The photograph was taken at a distance:
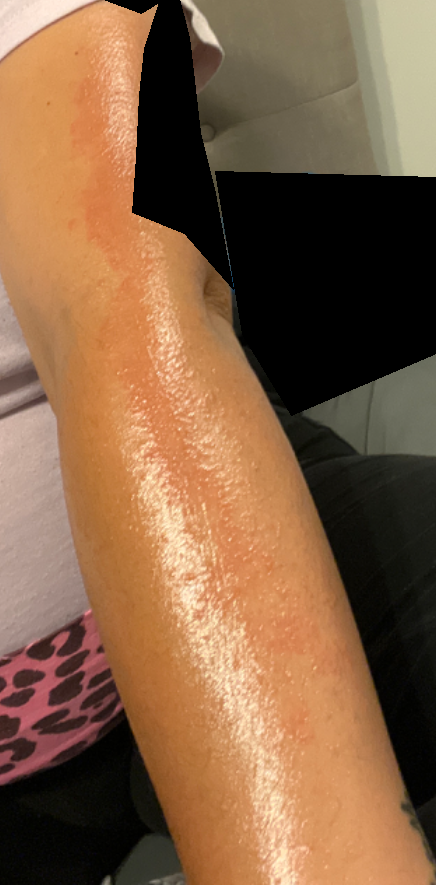Impression:
Acute dermatitis, NOS and Allergic Contact Dermatitis were considered with similar weight.